A dermoscopy image of a single skin lesion: 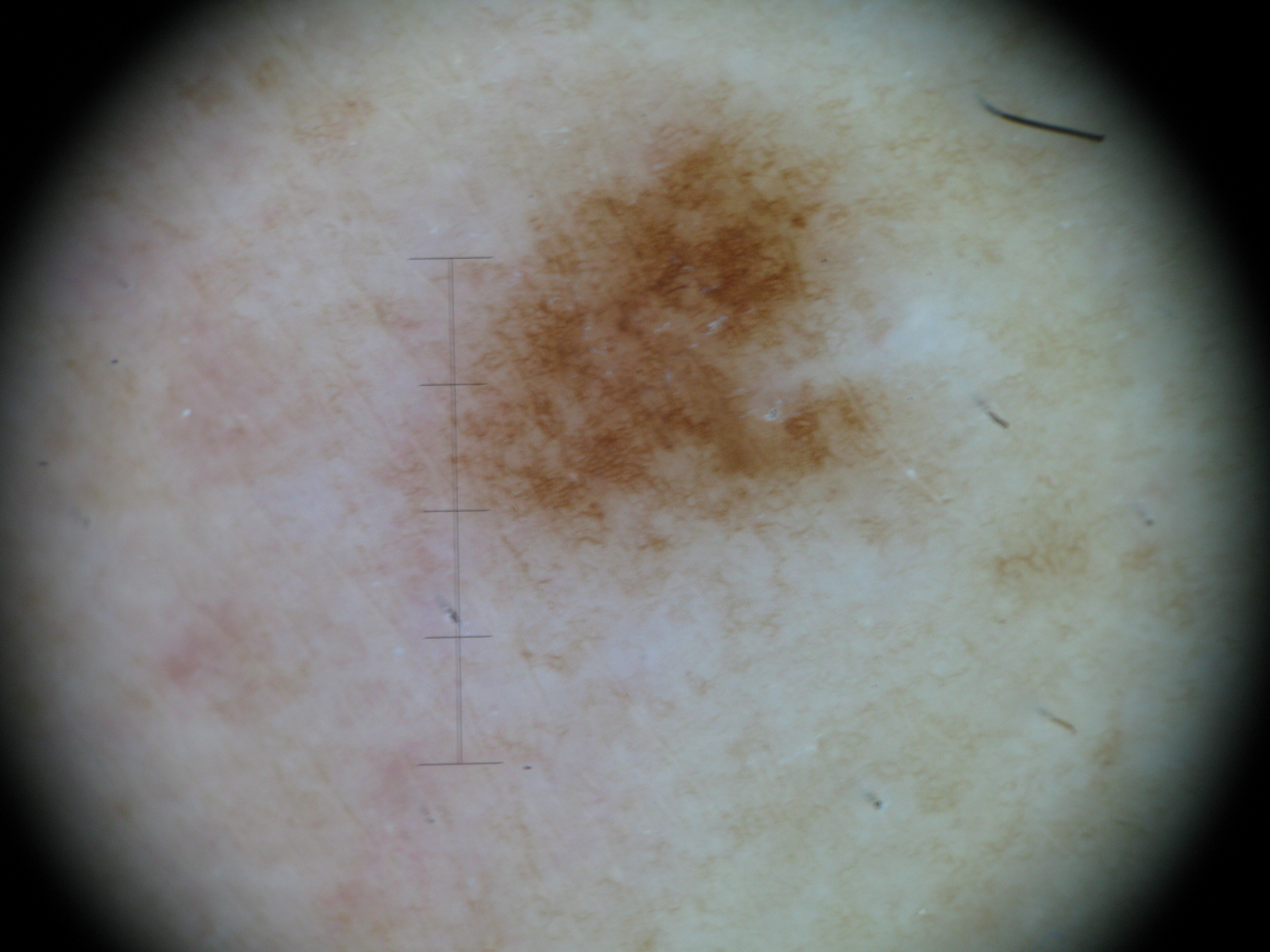{
  "diagnosis": {
    "name": "dysplastic junctional nevus",
    "code": "jd",
    "malignancy": "benign",
    "super_class": "melanocytic",
    "confirmation": "expert consensus"
  }
}